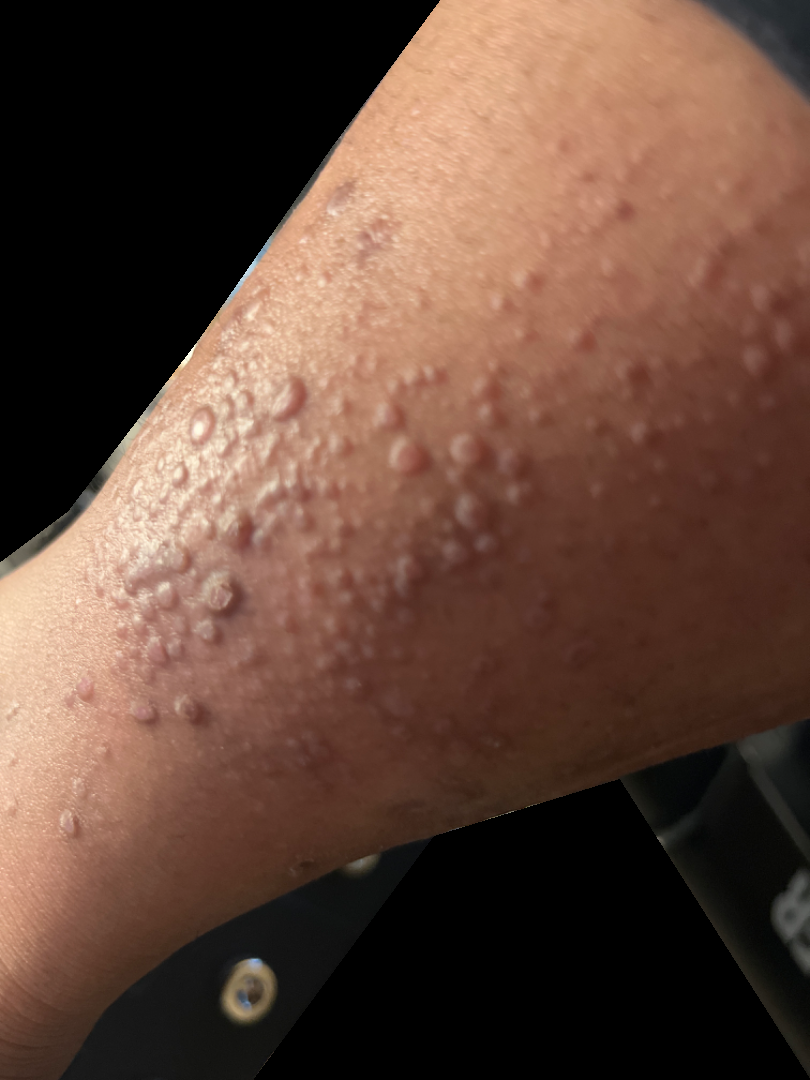This image was taken at an angle. Located on the leg. Self-categorized by the patient as a rash. The condition has been present for more than five years. Symptoms reported: itching. The lesion is described as fluid-filled and raised or bumpy. On photographic review by a dermatologist, Amyloidosis of skin (considered); Pretibial myxedema (considered); Lichen Simplex Chronicus (considered).